A close-up photograph. Female contributor, age 50–59 — 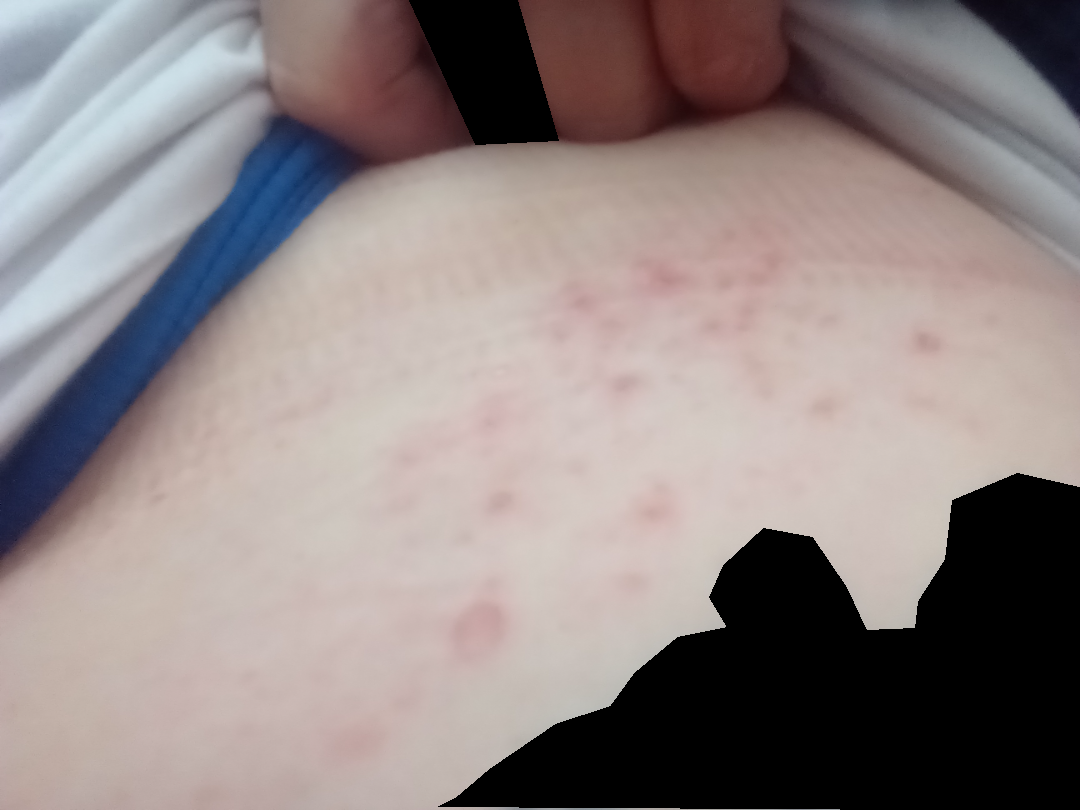The skin findings could not be characterized from the image.